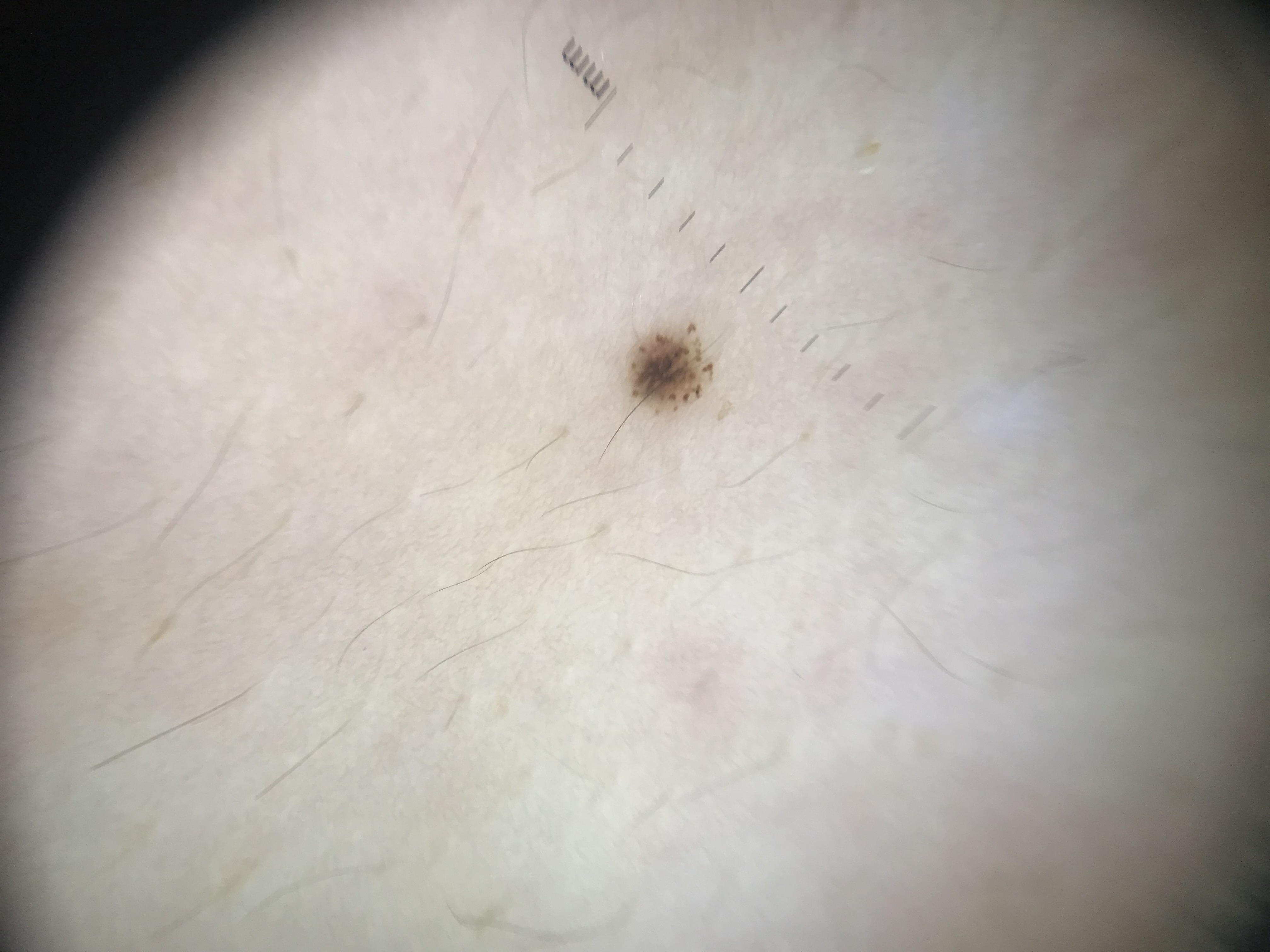A dermoscopy image of a single skin lesion.
Diagnosed as a benign lesion — a dysplastic junctional nevus.